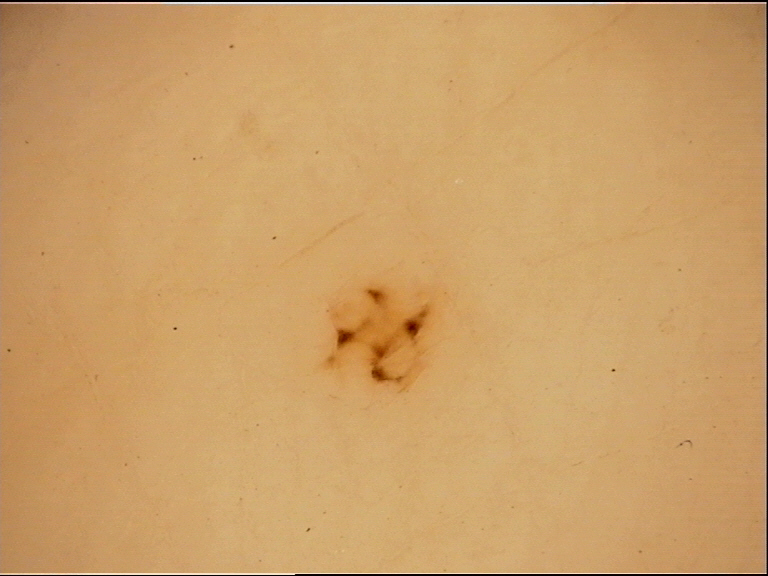Case:
A dermatoscopic image of a skin lesion. This is a banal lesion.
Conclusion:
Diagnosed as an acral junctional nevus.